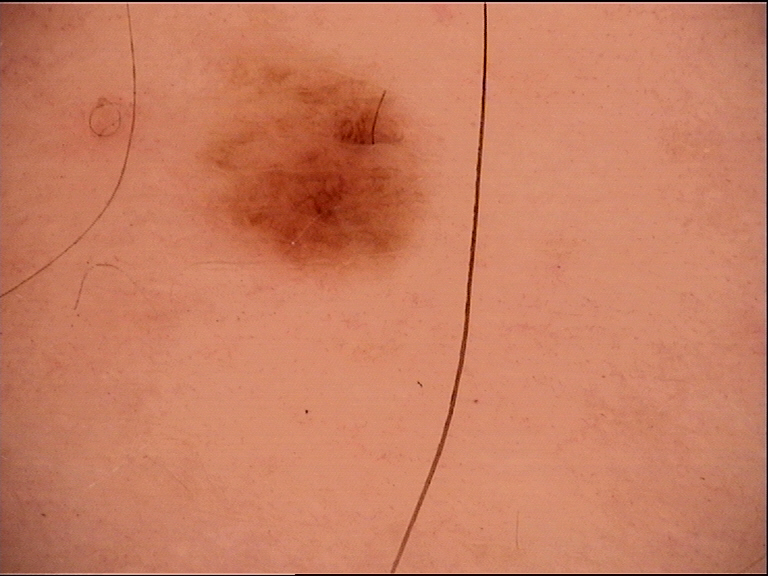A dermoscopic photograph of a skin lesion. Classified as a dysplastic junctional nevus.